Close-up view: 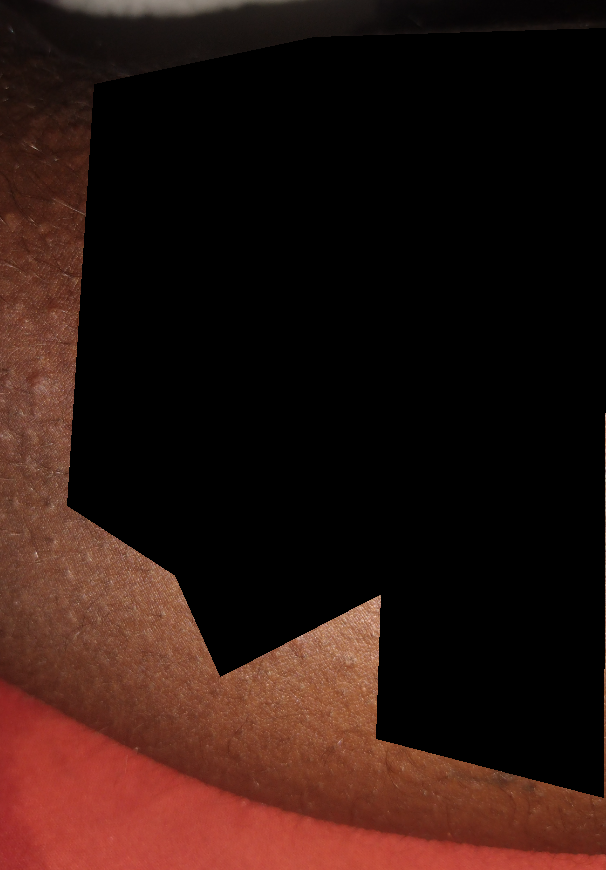Review:
The favored diagnosis is Lichen nitidus; also on the differential is Eczema; less likely is Keratosis pilaris.